A dermoscopic image of a skin lesion: 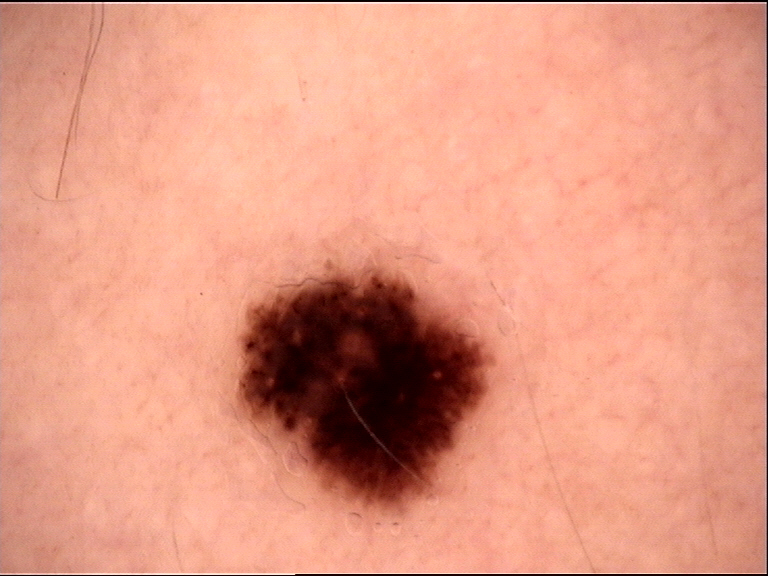Consistent with a benign lesion — a dysplastic junctional nevus.